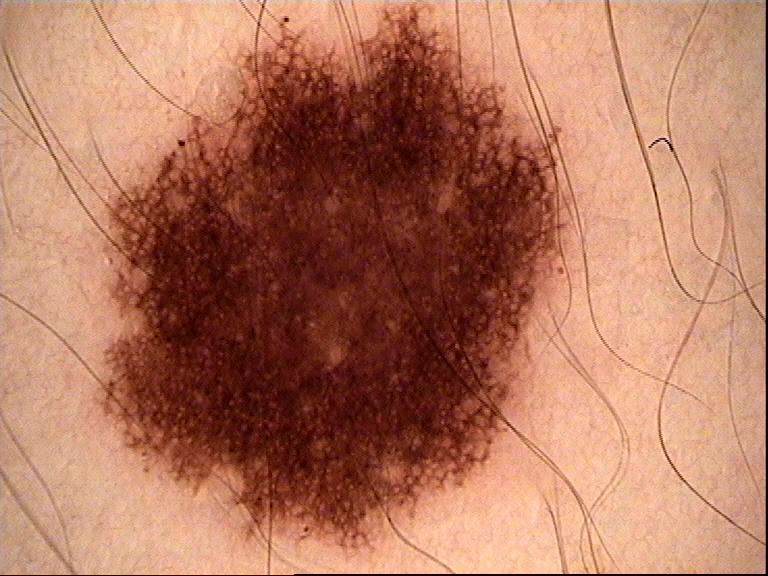The diagnostic label was a dysplastic compound nevus.